An image taken at an angle.
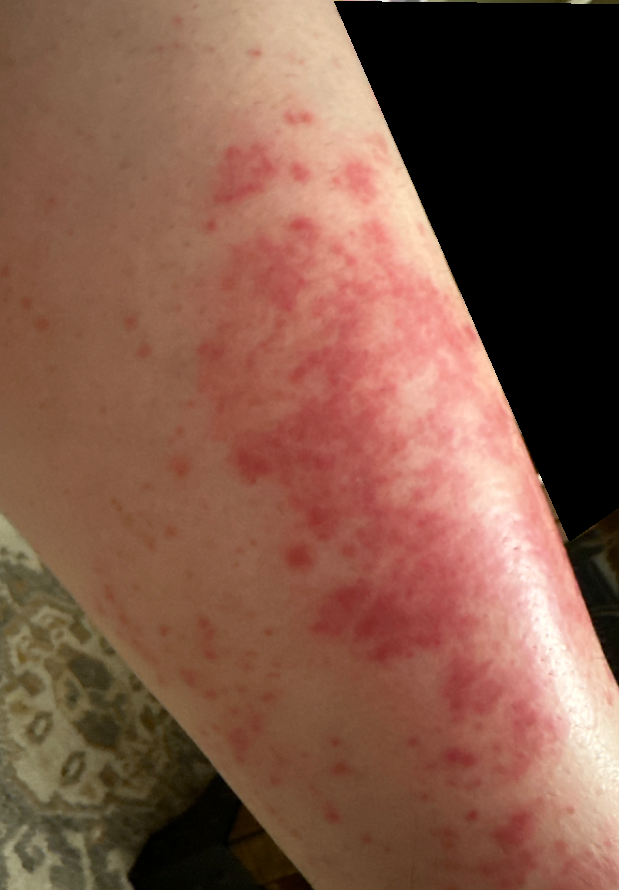<summary>
  <assessment>indeterminate</assessment>
  <skin_tone>
    <monk_skin_tone>2</monk_skin_tone>
  </skin_tone>
</summary>